Located on the arm, front of the torso, top or side of the foot, back of the torso and leg. A close-up photograph. The patient is a male aged 40–49.
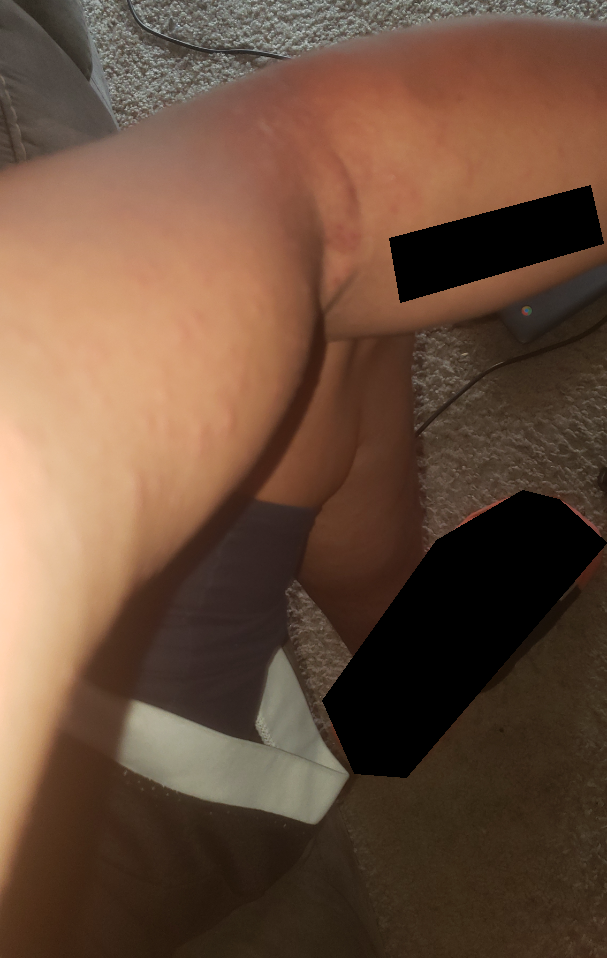| field | value |
|---|---|
| impression | Folliculitis and Insect Bite were each considered, in no particular order |